A skin lesion imaged with a dermatoscope.
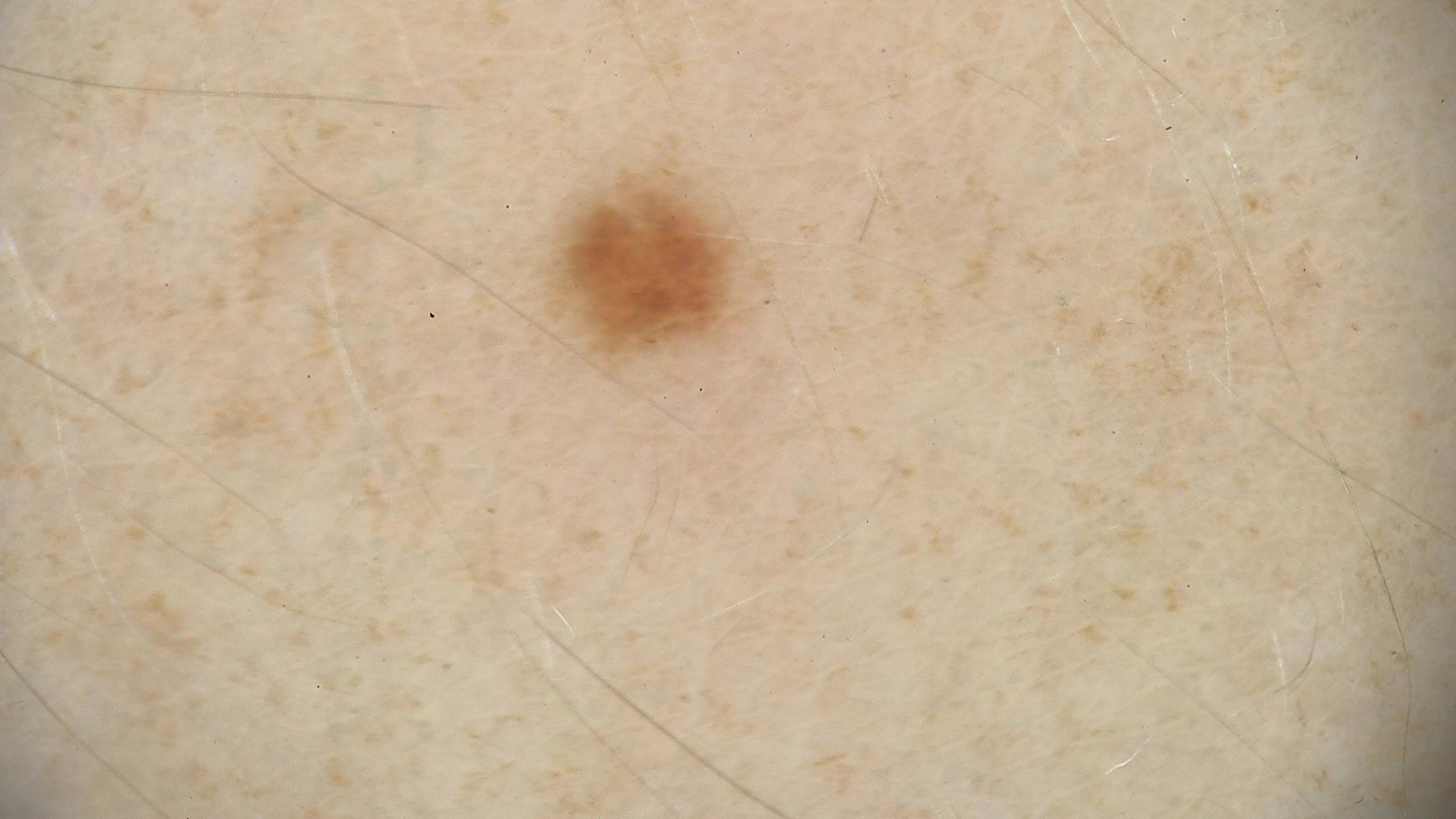{"diagnosis": {"name": "dysplastic junctional nevus", "code": "jd", "malignancy": "benign", "super_class": "melanocytic", "confirmation": "expert consensus"}}